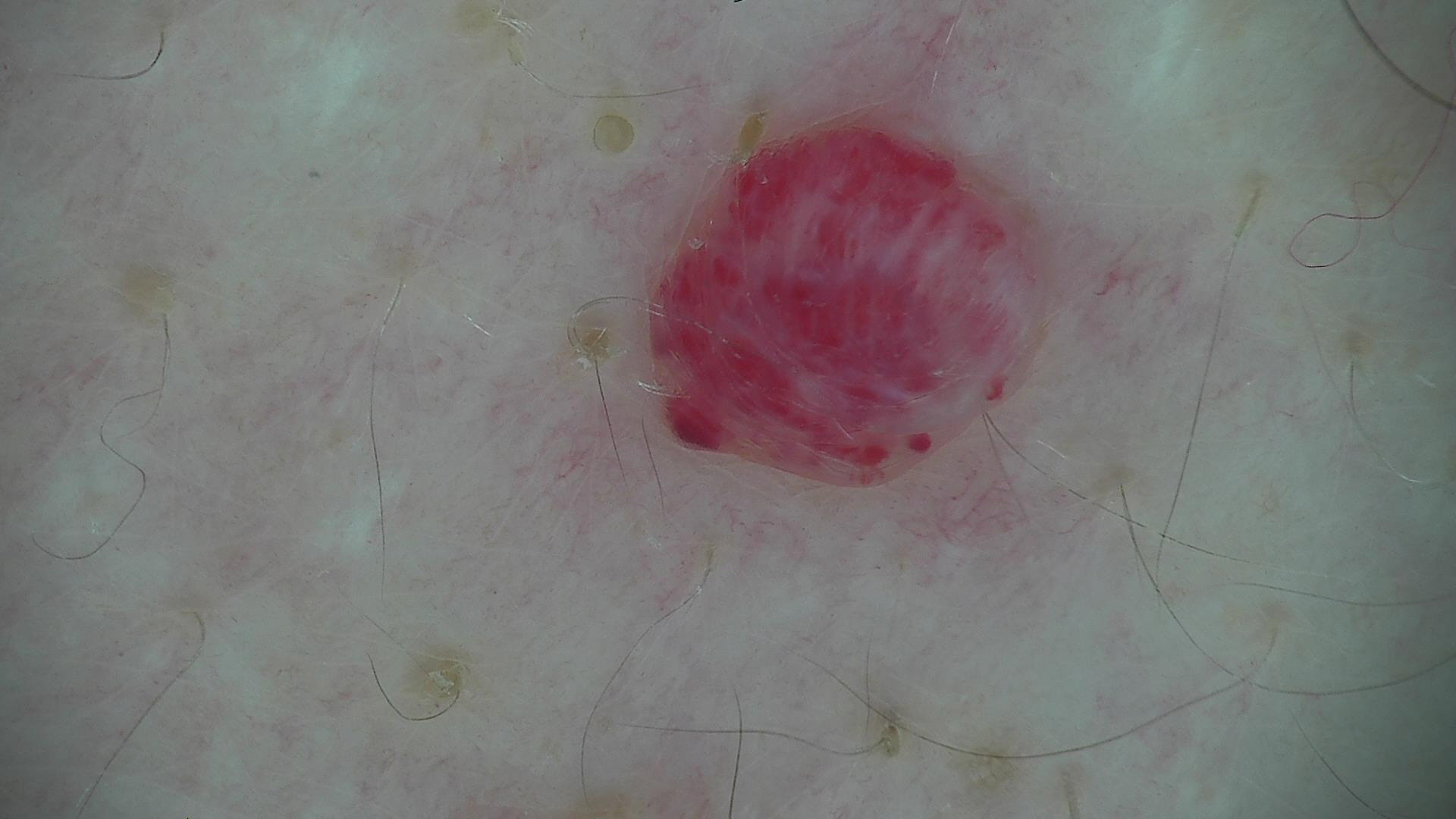Findings:
A dermoscopic close-up of a skin lesion. The architecture is that of a vascular lesion.
Impression:
Diagnosed as a hemangioma.